A dermoscopic image of a skin lesion.
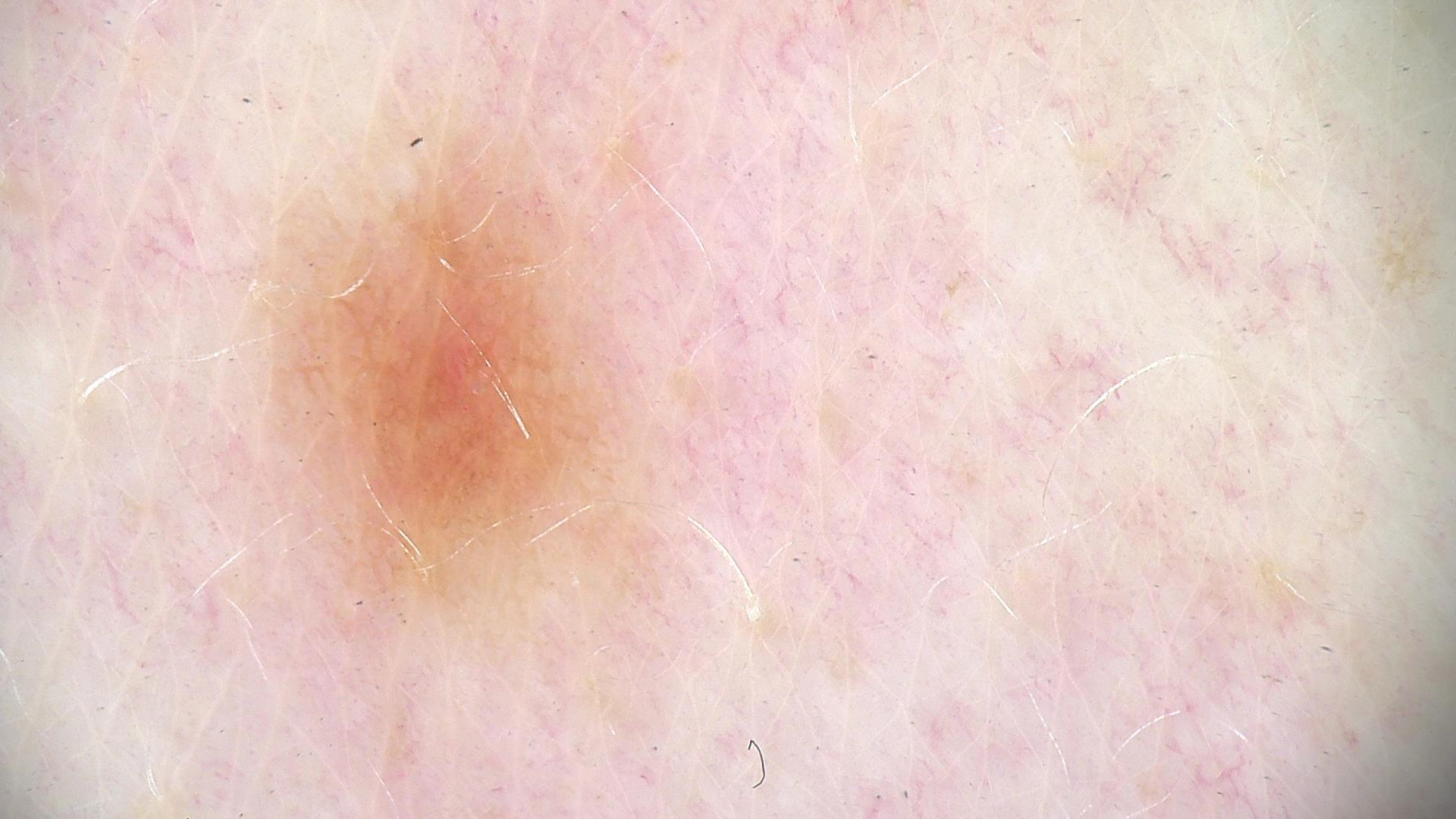Diagnosed as a dysplastic junctional nevus.